The patient says their skin reddens with sun exposure. A macroscopic clinical photograph of a skin lesion. Referred with a clinical suspicion of basal cell carcinoma. Few moles overall by the patient's own estimate. By self-report, a personal history of skin cancer, a personal history of cancer, and no prior organ transplant. A male subject age 76.
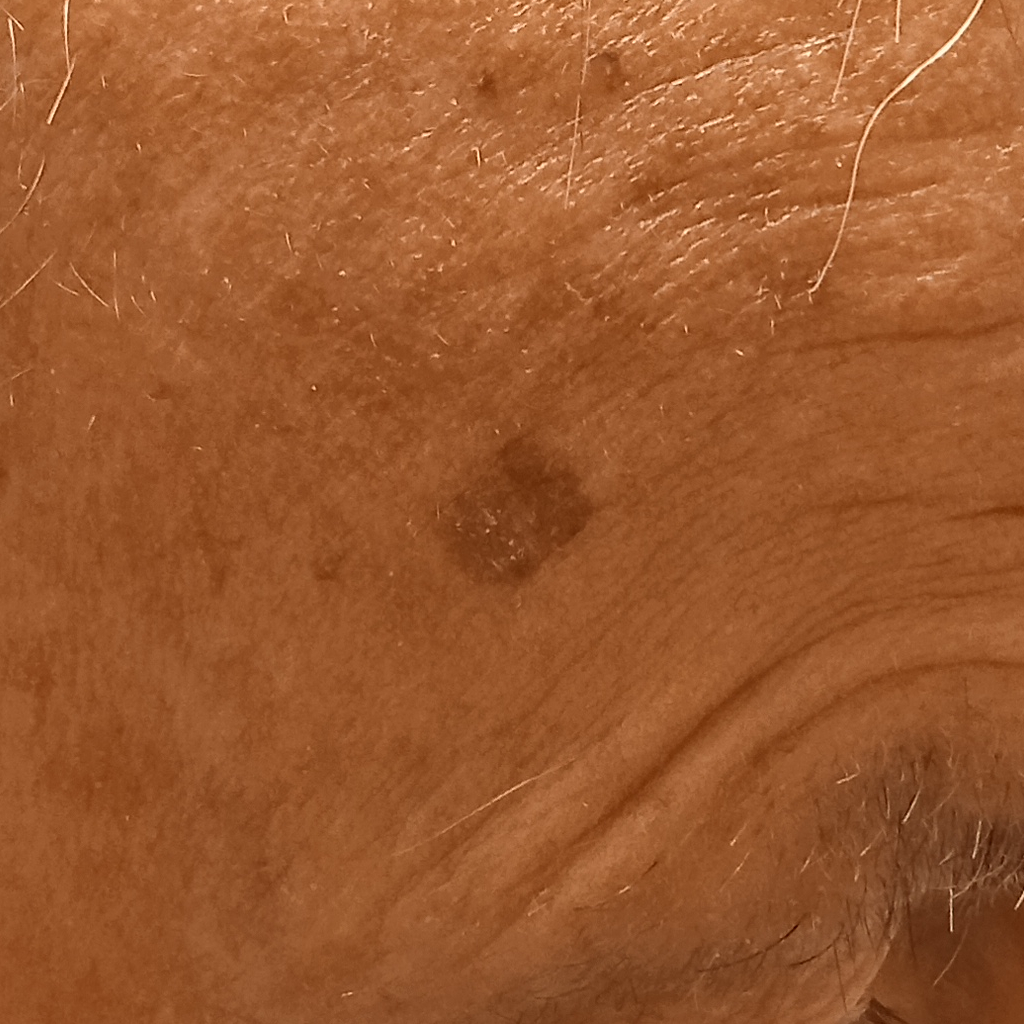The lesion is about 8.7 mm across. On biopsy, the diagnosis was a basal cell carcinoma, following excision, with a measured thickness of 2.5 mm.